The subject is 18–29, female. Human graders estimated a MST of 2. The affected area is the back of the torso, front of the torso and leg. The photo was captured at an angle. Texture is reported as raised or bumpy. The patient reported no systemic symptoms. The patient notes burning and itching. The patient considered this skin that appeared healthy to them.
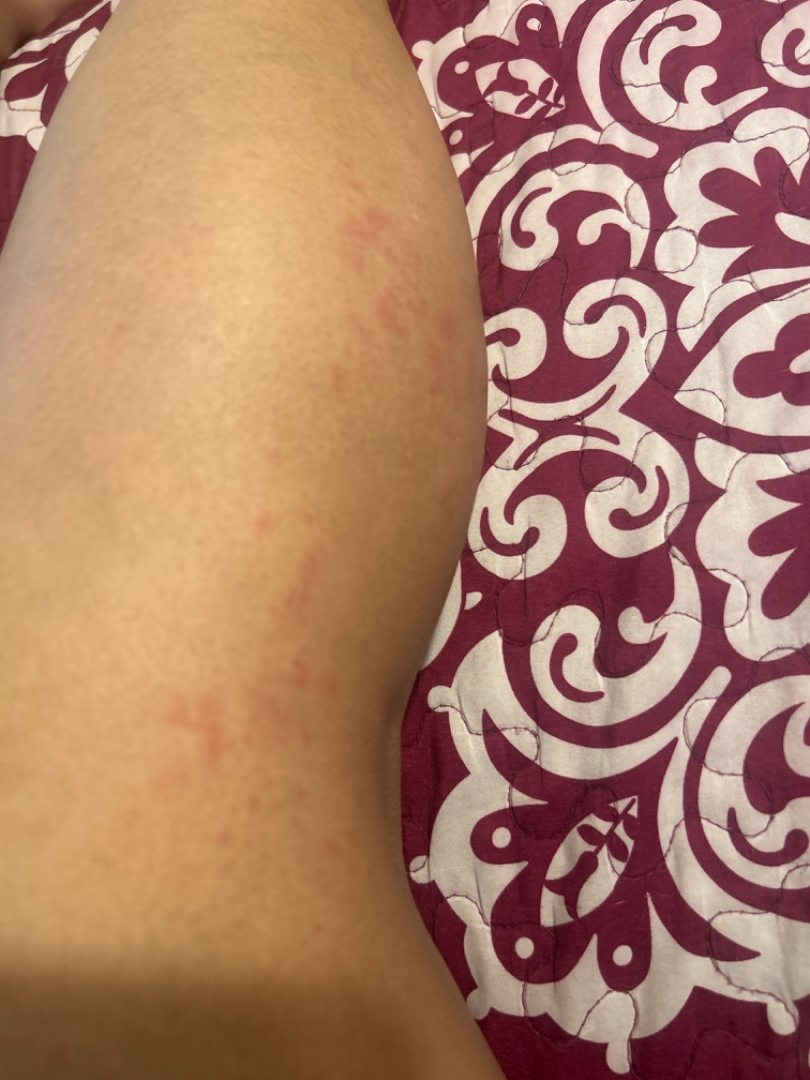differential diagnosis: the leading consideration is Allergic Contact Dermatitis; less likely is Eczema; less probable is Dermatitis herpetiformis; a remote consideration is Insect Bite; lower on the differential is Folliculitis.